A dermoscopic image of a skin lesion.
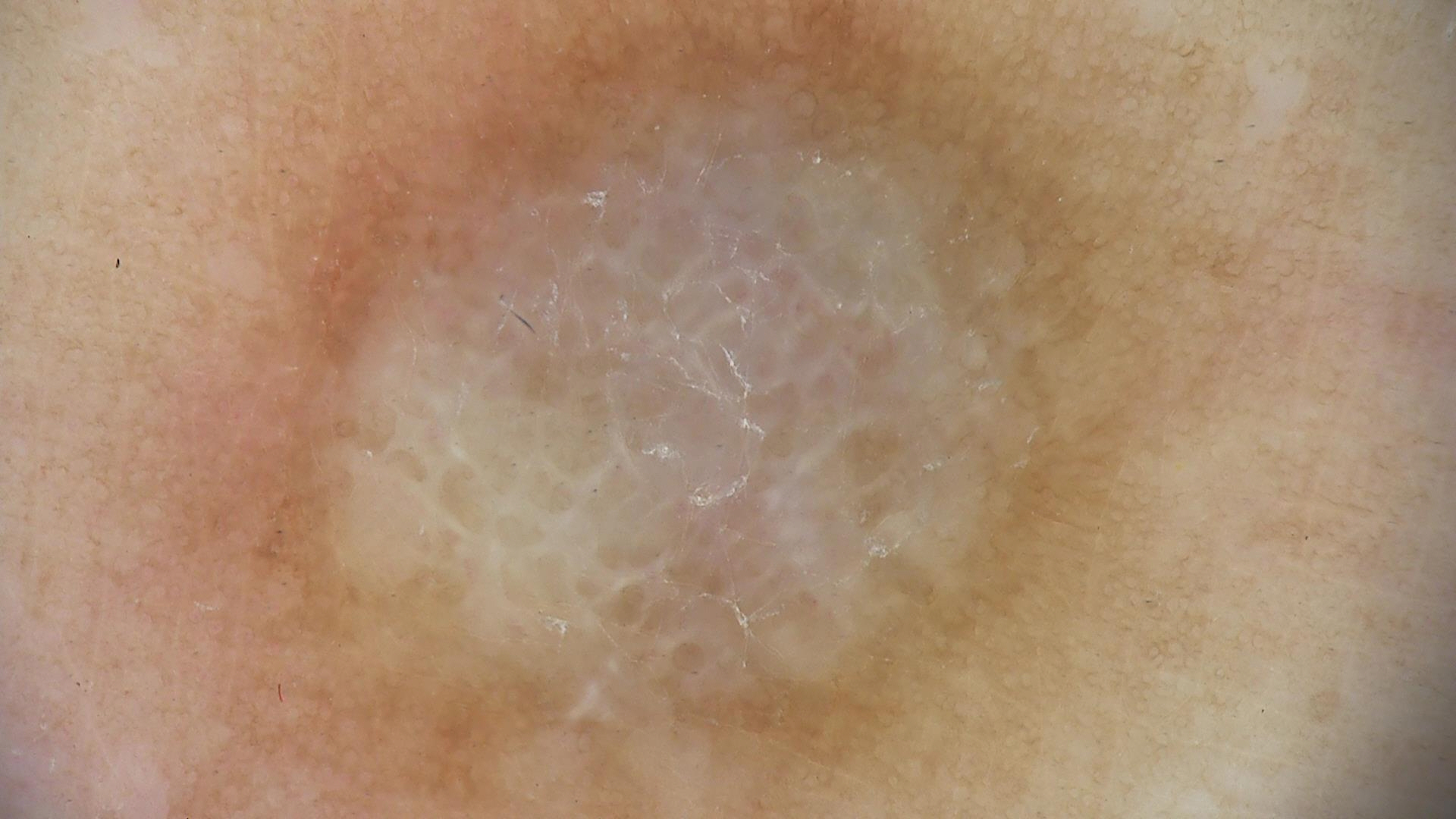| key | value |
|---|---|
| label | dermatofibroma (expert consensus) |